The photograph is a close-up of the affected area, reported duration is less than one week, located on the front of the torso, symptoms reported: itching, the contributor reports the lesion is raised or bumpy: 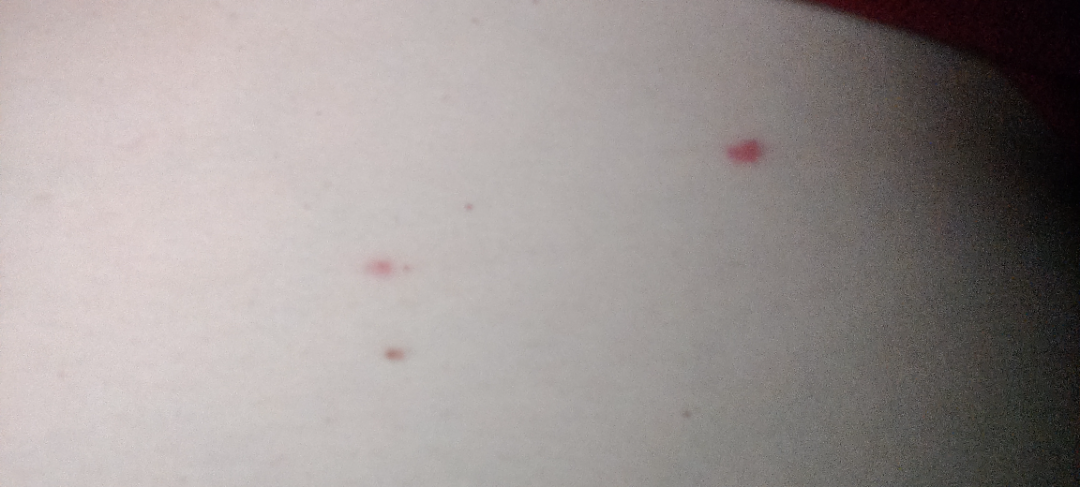{
  "assessment": "unable to determine"
}